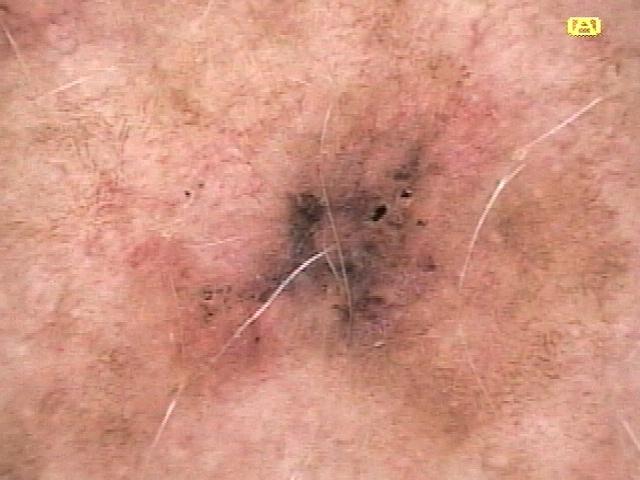| field | value |
|---|---|
| subject | female, in their mid- to late 60s |
| modality | dermoscopic image |
| body site | the posterior trunk |
| pathology | Melanoma (biopsy-proven) |